A clinical close-up photograph of a skin lesion · a female patient 70 years of age:
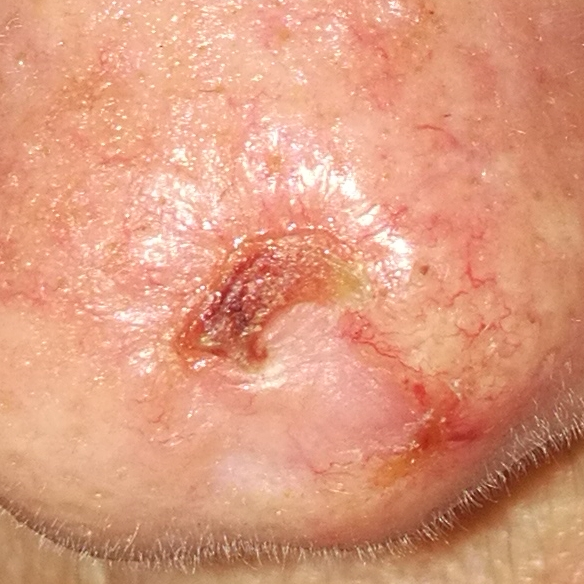  lesion_location: the nose
  symptoms:
    present:
      - pain
      - itching
      - bleeding
      - elevation
      - growth
  diagnosis:
    name: basal cell carcinoma
    code: BCC
    malignancy: malignant
    confirmation: histopathology